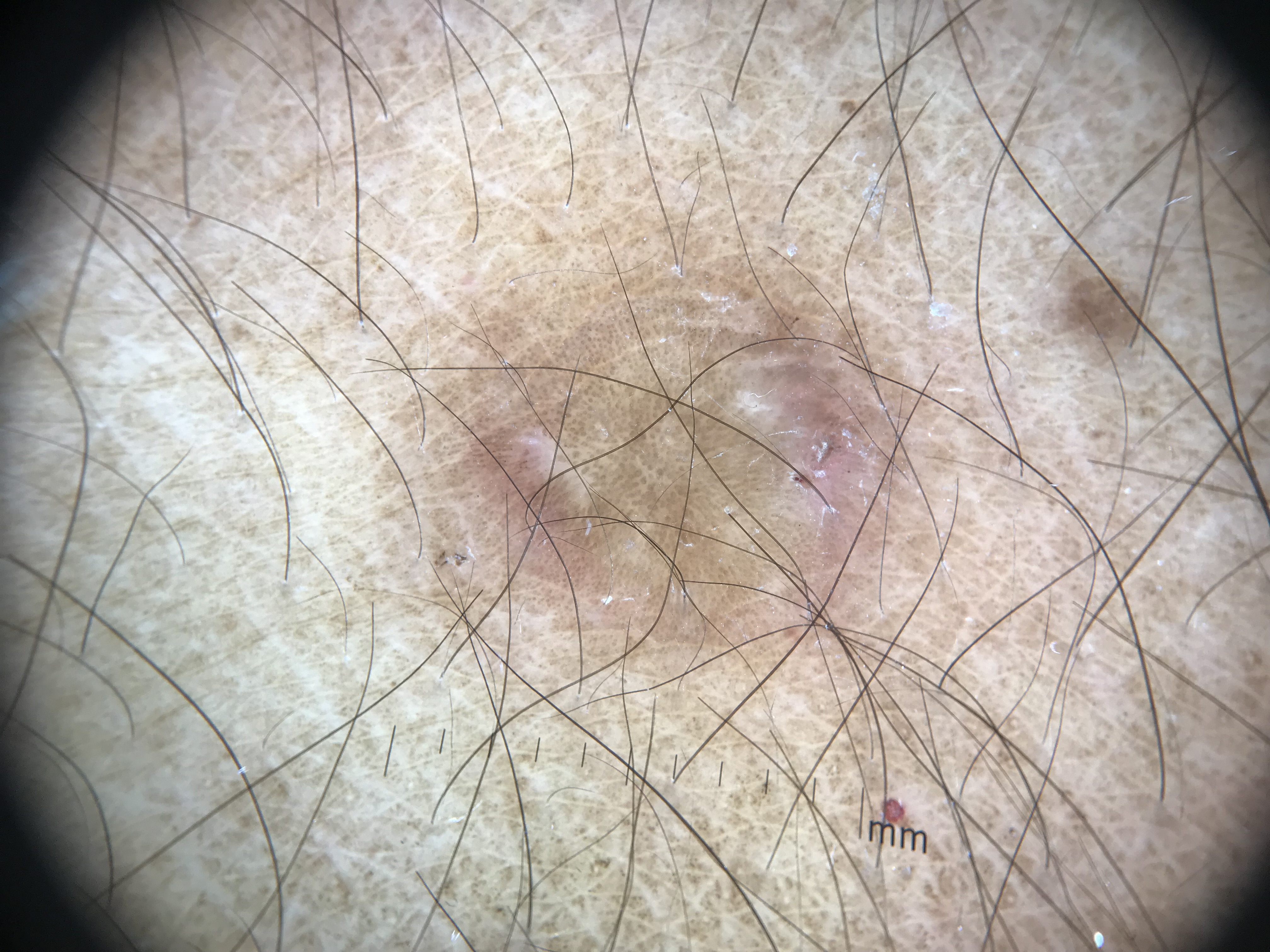A dermoscopic image of a skin lesion.
Classified as a dermatofibroma.